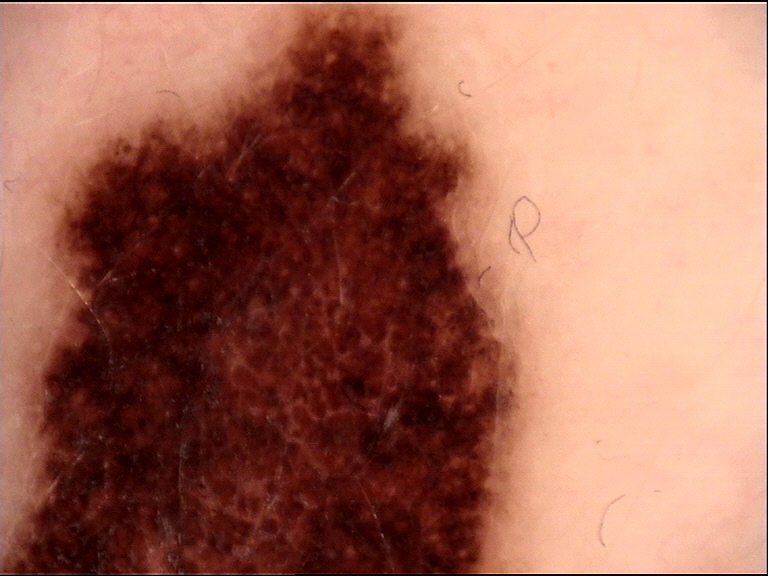diagnosis:
  name: congenital compound nevus
  code: ccb
  malignancy: benign
  super_class: melanocytic
  confirmation: expert consensus